A male patient aged 43-47 · a dermoscopic image of a skin lesion: 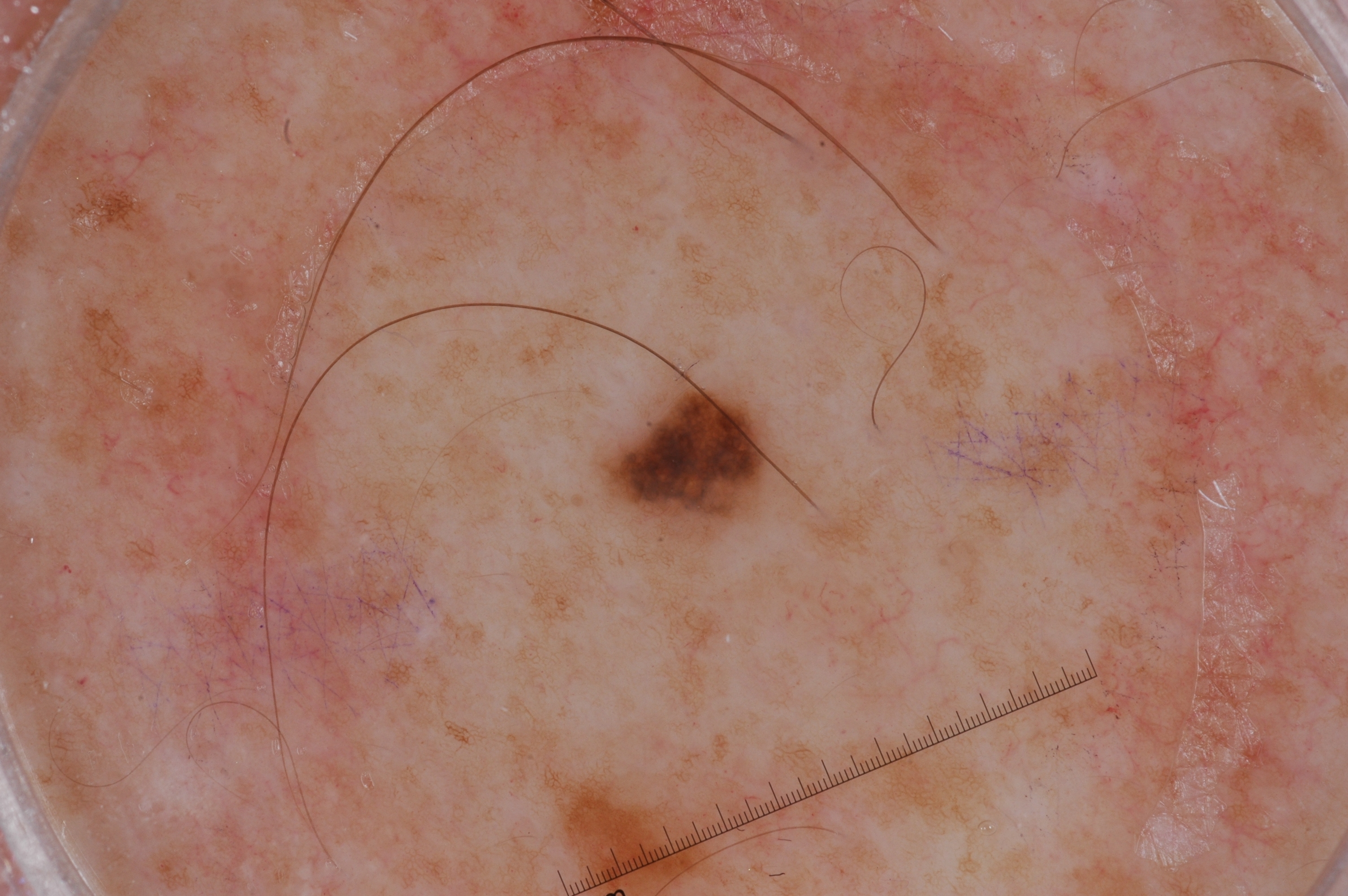dermoscopic features = pigment network; absent: negative network, milia-like cysts, and streaks | size = small | lesion bbox = <box>599, 383, 767, 537</box> | diagnosis = a melanocytic nevus, a benign skin lesion.